Symptoms reported: bothersome appearance; no relevant systemic symptoms; the photograph was taken at an angle; the arm is involved; self-categorized by the patient as a rash; the subject is female; texture is reported as flat: 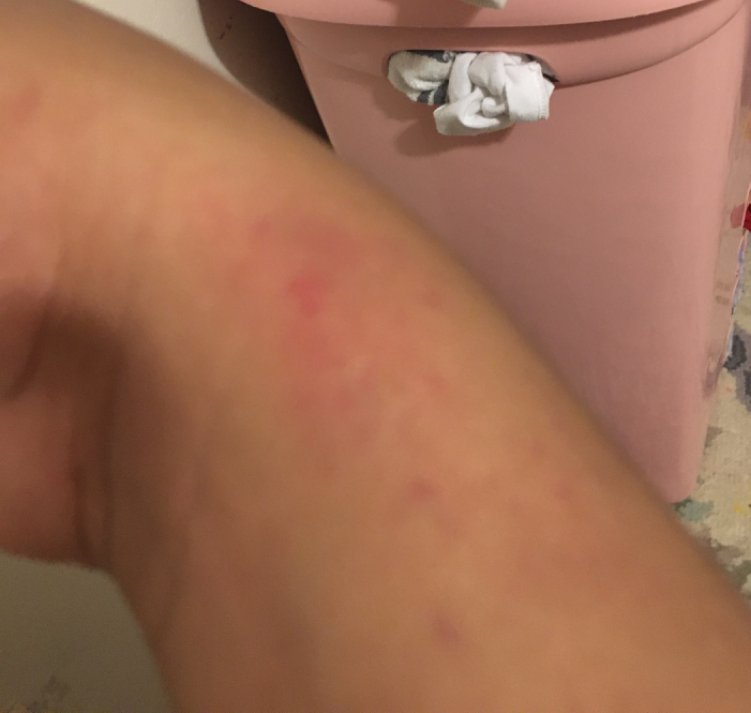On dermatologist assessment of the image, most consistent with Irritant Contact Dermatitis.